A smartphone photograph of a skin lesion · a subject 50 years old.
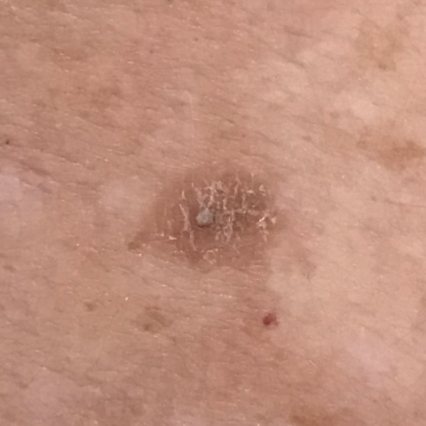| field | value |
|---|---|
| site | an arm |
| diagnostic label | actinic keratosis (clinical consensus) |